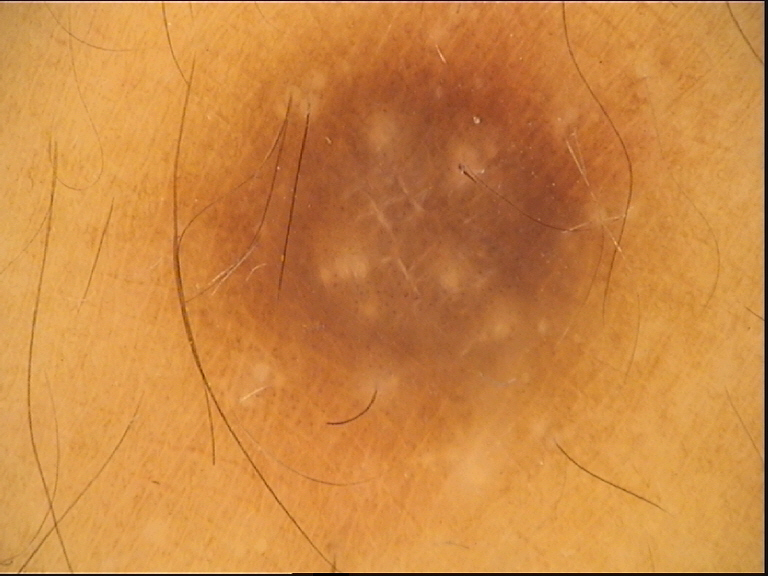A dermoscopic image of a skin lesion.
Consistent with a dermatofibroma.